The affected area is the back of the torso and front of the torso · the photograph is a close-up of the affected area: 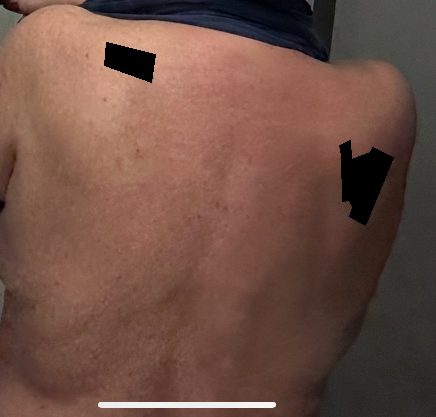lesion symptoms: itching
lesion texture: flat
present for: one to four weeks
diagnostic considerations: most likely Drug Rash; also on the differential is Eczema